The photograph was taken at a distance: 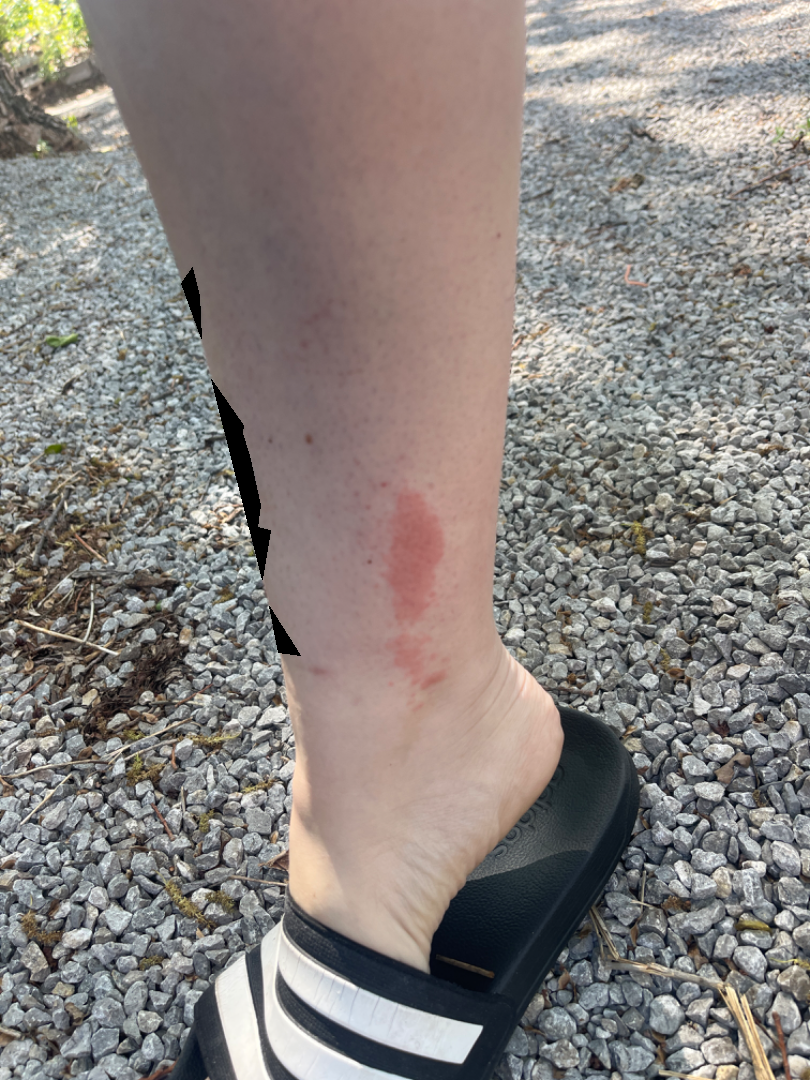differential:
  tied_lead:
    - Allergic Contact Dermatitis
    - Irritant Contact Dermatitis